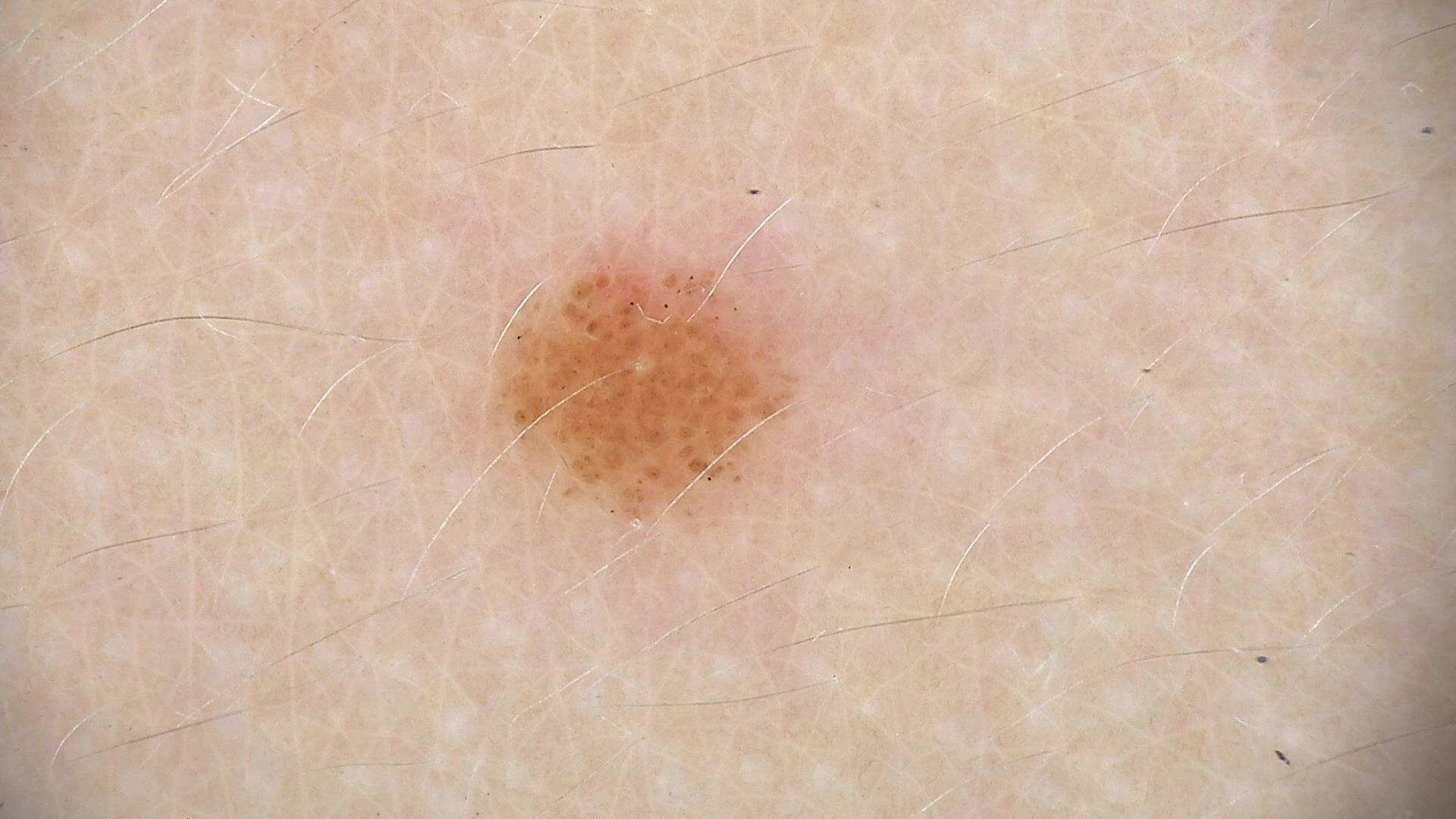Findings:
Dermoscopy of a skin lesion.
Conclusion:
The diagnostic label was a dysplastic junctional nevus.